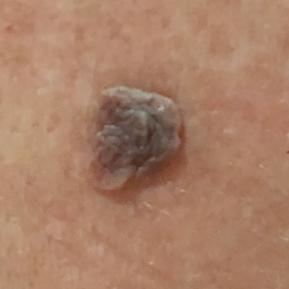Conclusion: Diagnosed by dermatologist consensus as a nevus.